A dermoscopic image of a skin lesion:
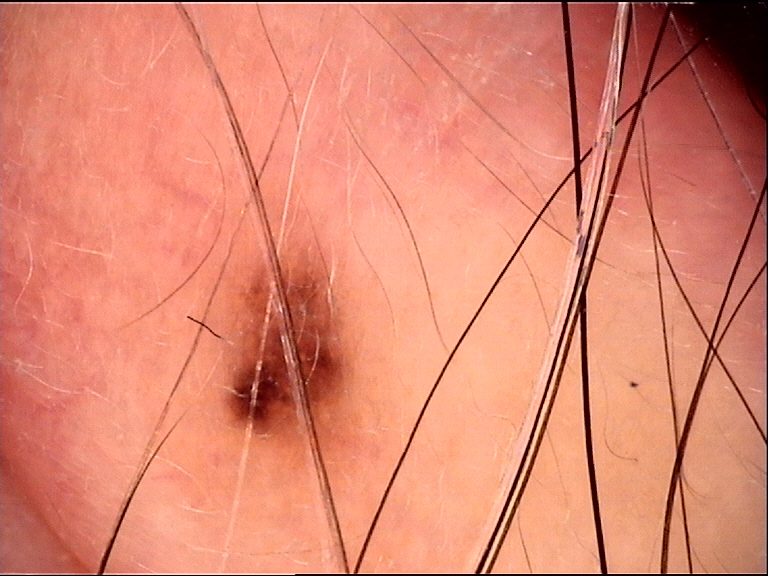The diagnosis was a dysplastic junctional nevus.